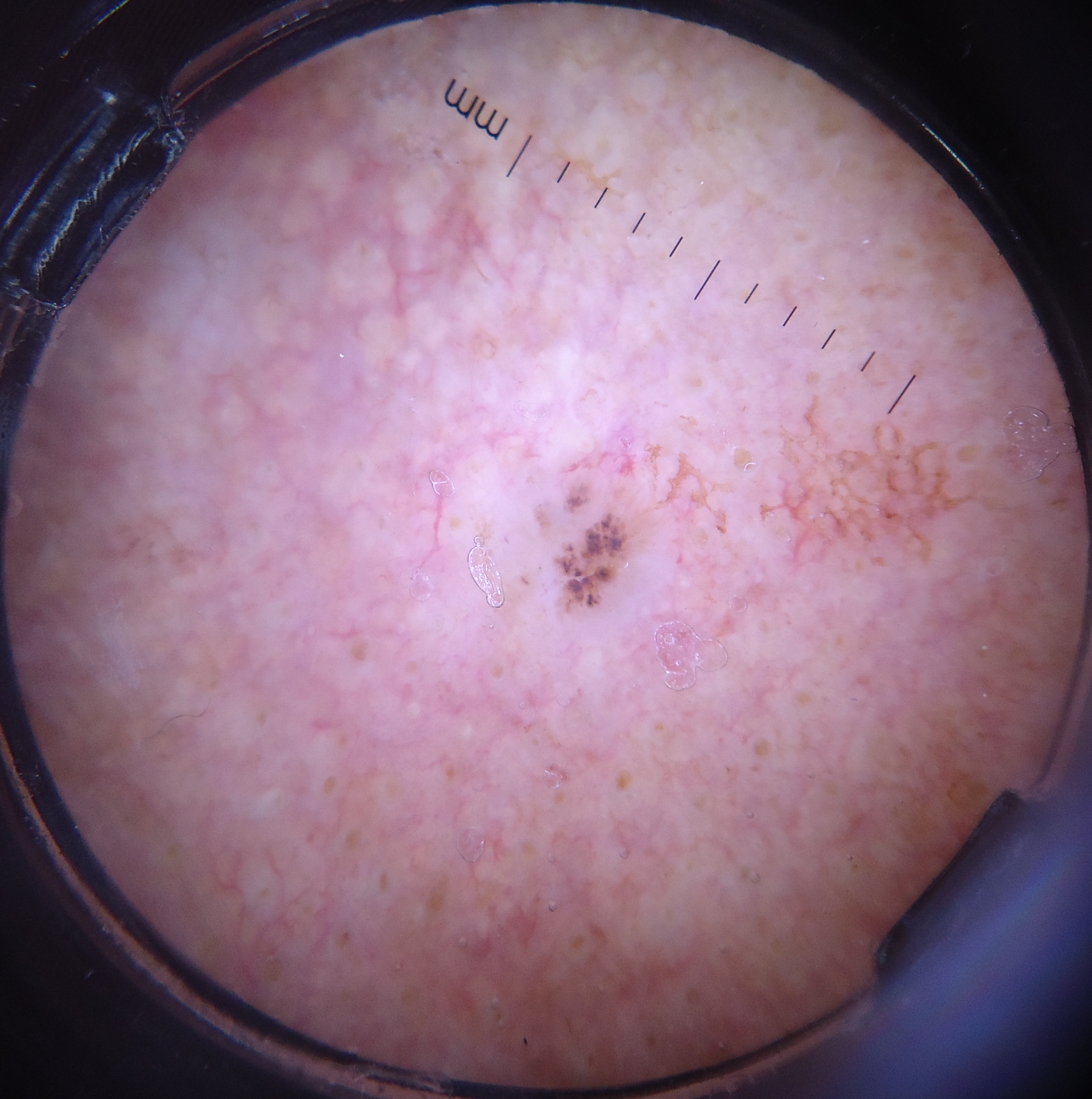label = basal cell carcinoma (biopsy-proven).